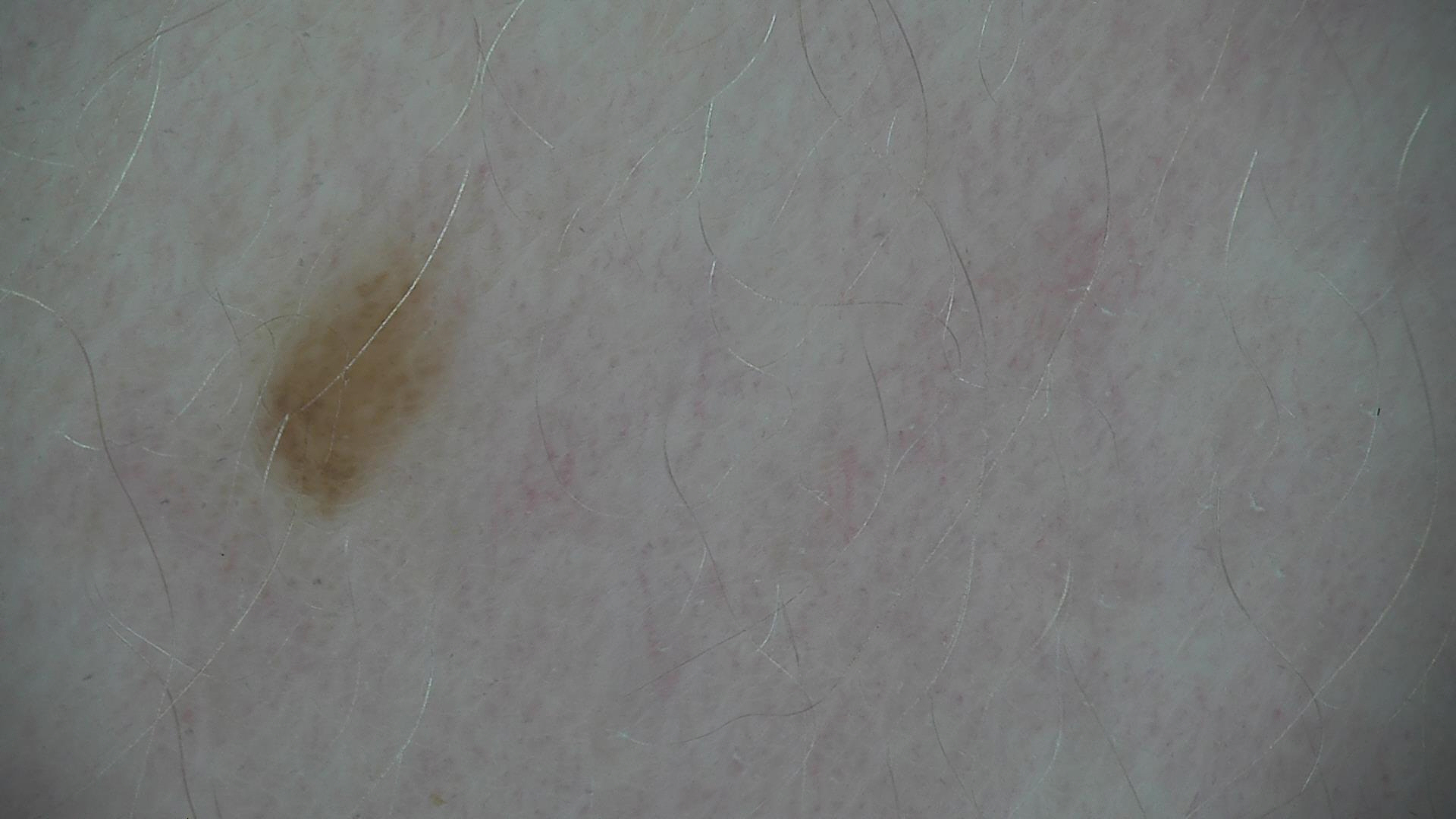Diagnosed as a junctional nevus.